A dermoscopic image of a skin lesion:
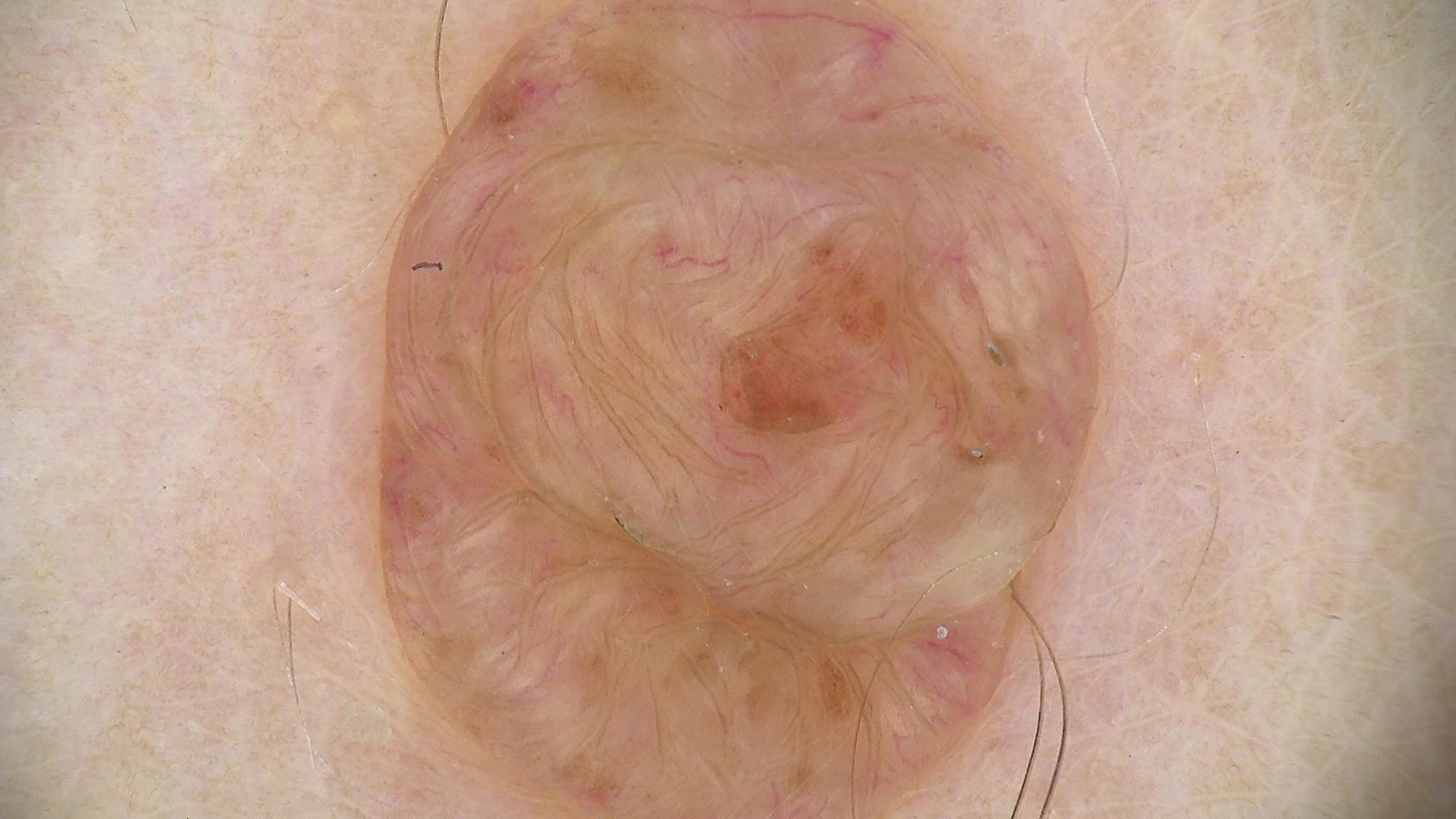lesion type = banal, class = dermal nevus (expert consensus).